This is a dermoscopic photograph of a skin lesion — 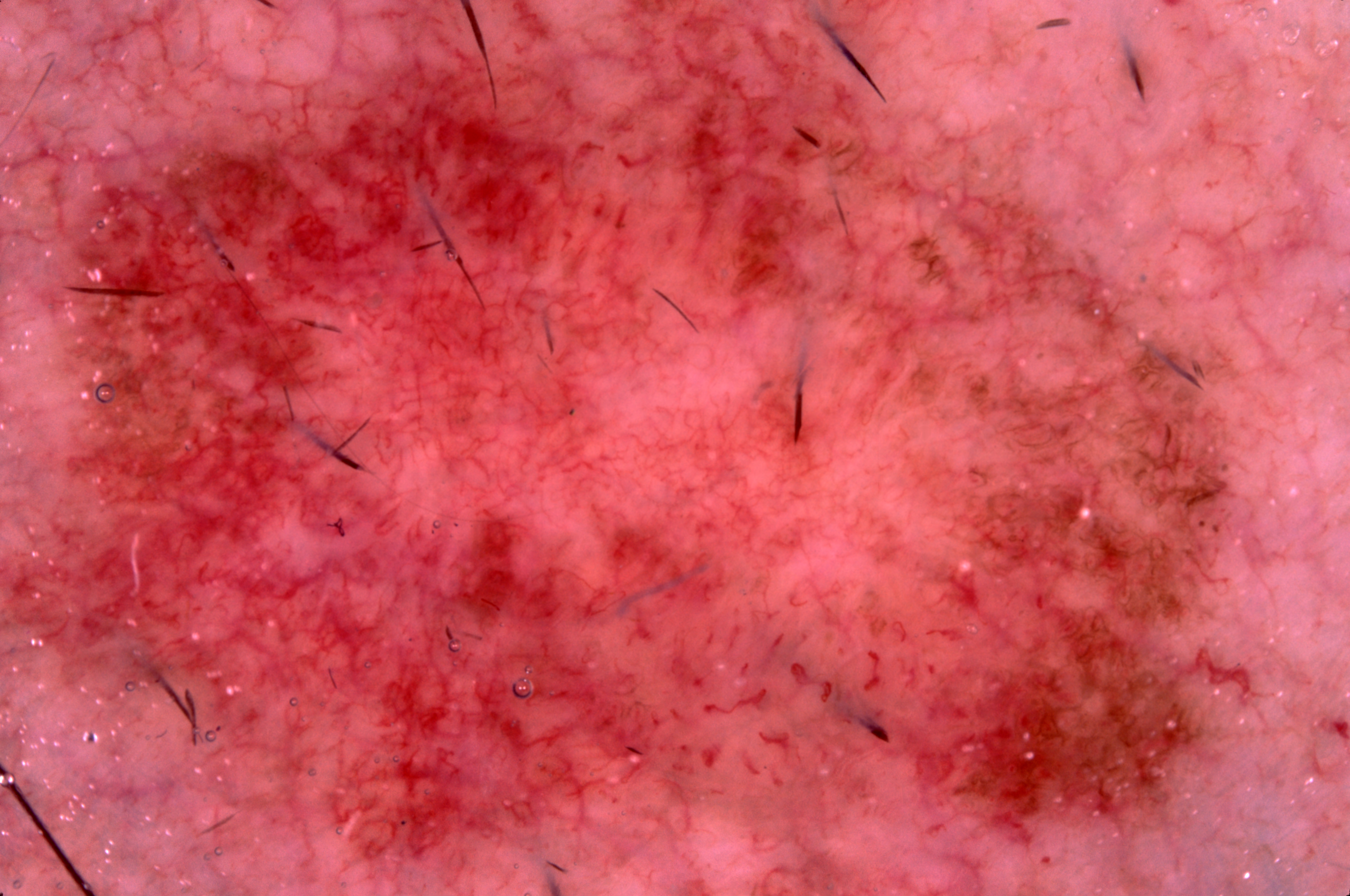Case summary:
The lesion stretches across essentially the whole frame. Dermoscopic review identifies milia-like cysts and pigment network.
Conclusion:
Confirmed on histopathology as a melanoma, a malignant lesion.